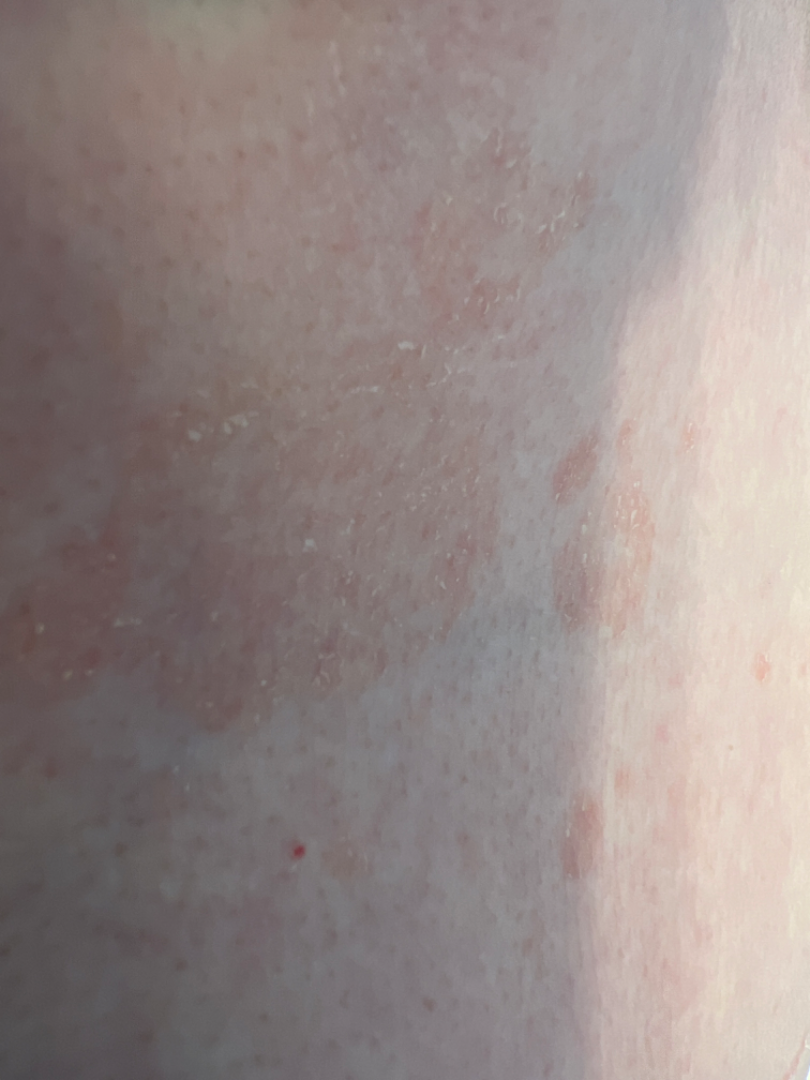Findings:
The case was difficult to assess from the available photograph.
Background:
An image taken at an angle.